A dermatoscopic image of a skin lesion: 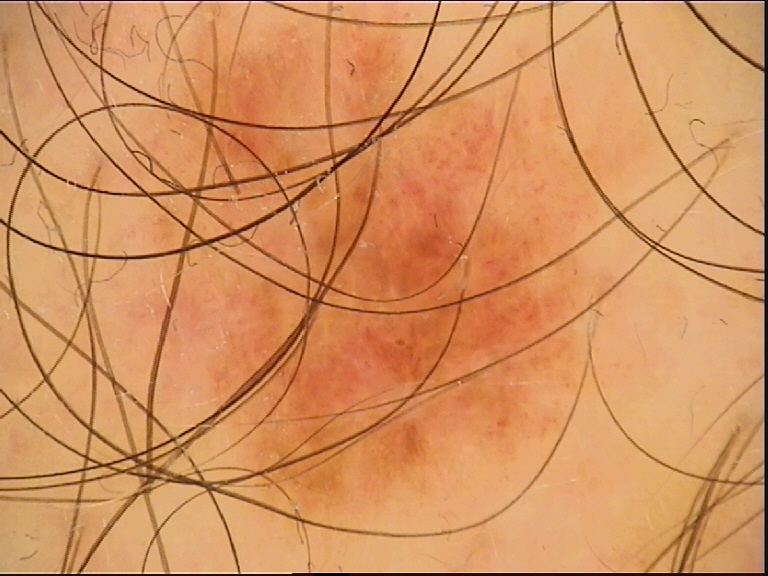Consistent with a benign lesion — a dysplastic compound nevus.